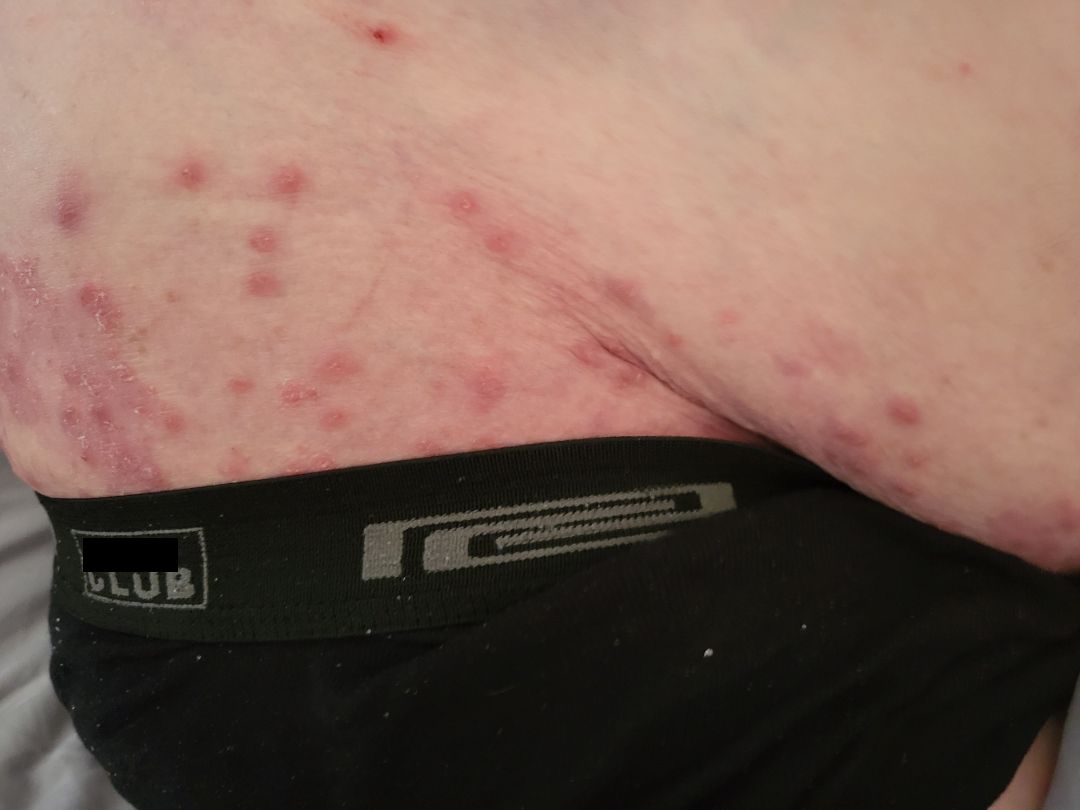Notes:
– present for — about one day
– symptoms — bleeding and itching
– self-categorized as — a rash
– location — back of the torso
– image framing — close-up
– diagnostic considerations — reviewed remotely by one dermatologist: the primary impression is Tinea; also raised was Impetigo; the differential also includes Folliculitis